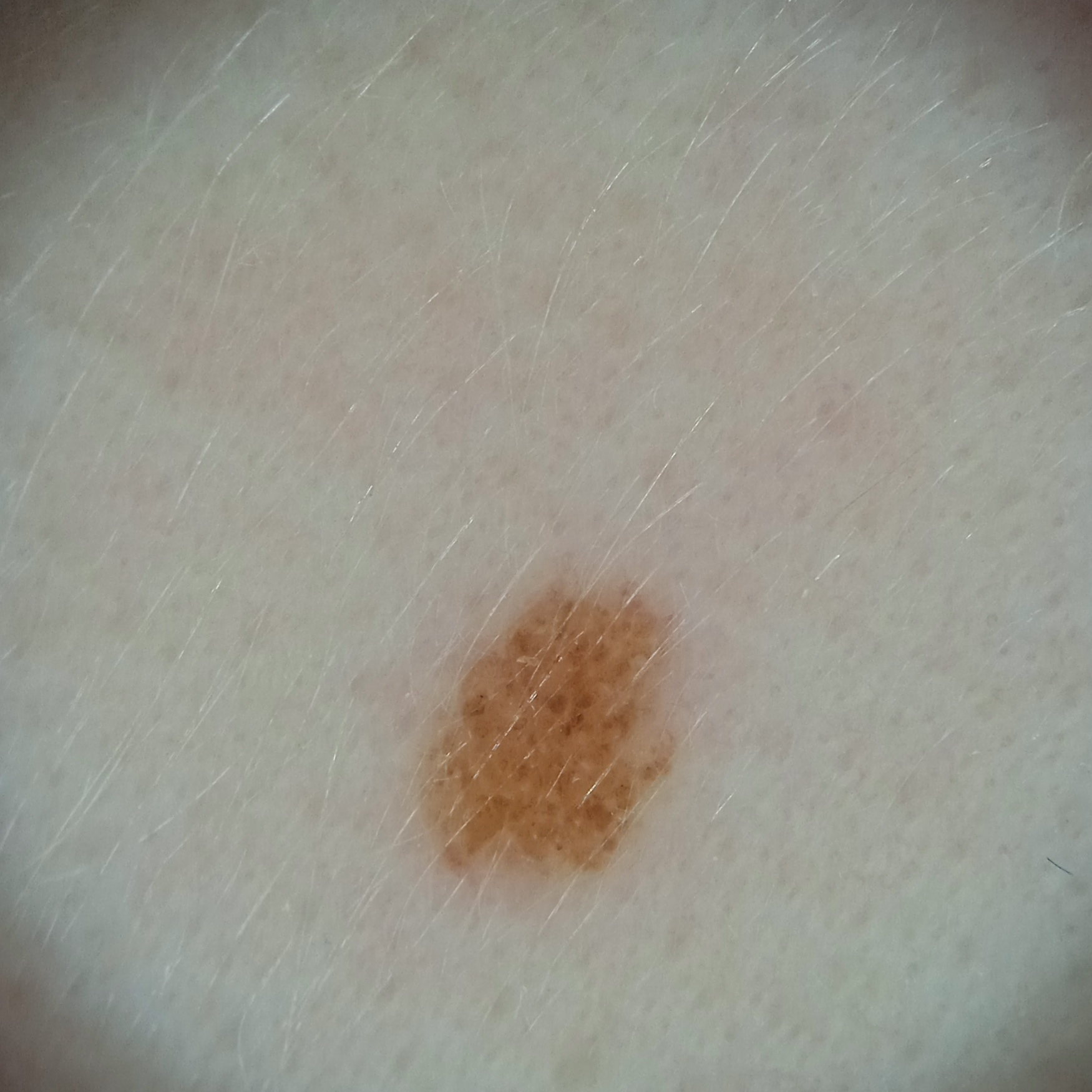Q: How does the patient's skin react to sun?
A: skin reddens with sun exposure
Q: What is the patient's nevus burden?
A: few melanocytic nevi overall
Q: Why was this imaged?
A: research study (no referral diagnosis)
Q: What is the anatomic site?
A: the face
Q: What was the diagnosis?
A: melanocytic nevus (dermatologist consensus)